A male subject, aged 63 to 67 · a dermatoscopic image of a skin lesion:
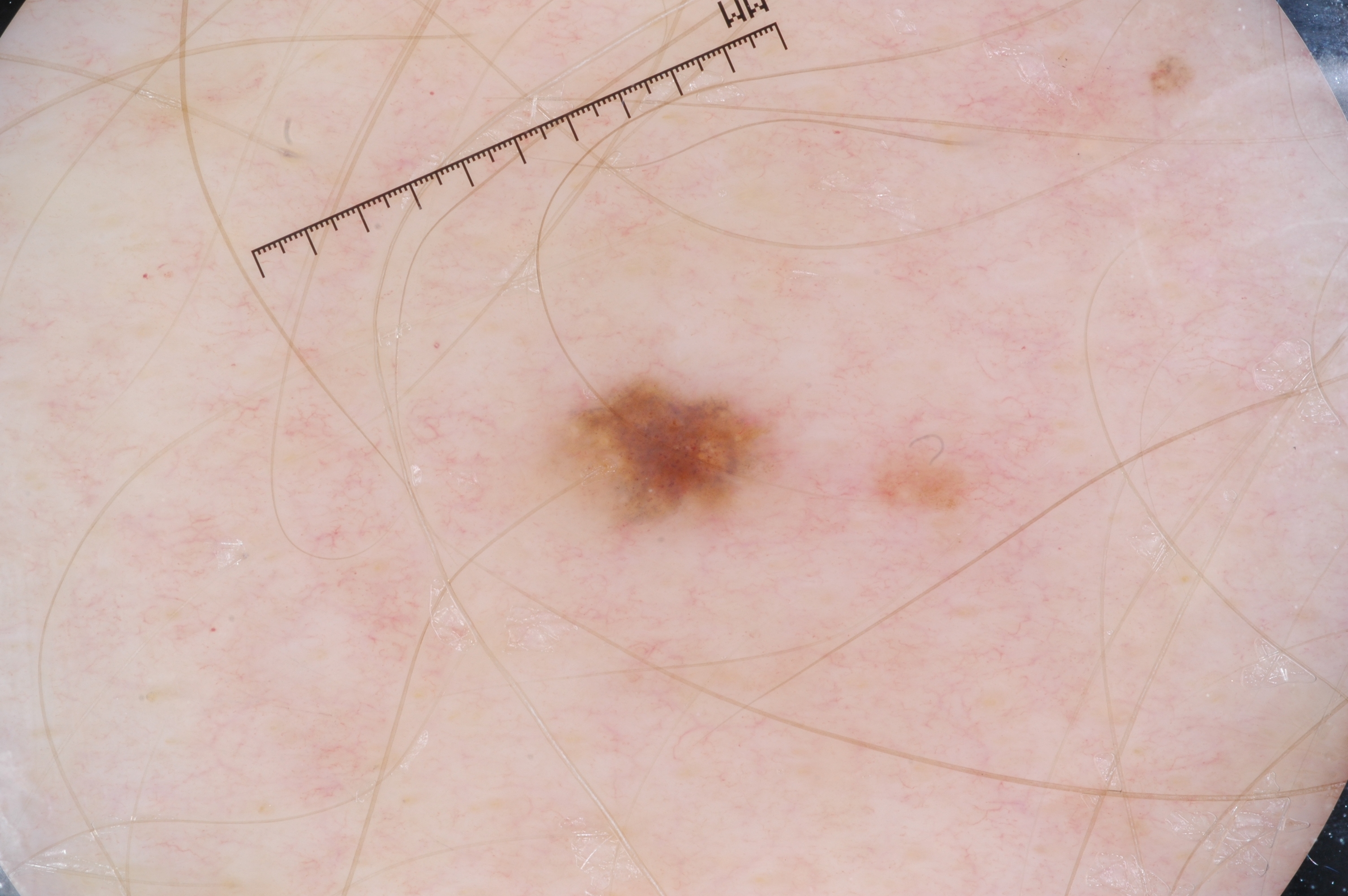Q: What is the lesion's bounding box?
A: <box>548, 371, 779, 532</box>
Q: How large is the lesion within the image?
A: small
Q: What does dermoscopy show?
A: milia-like cysts; absent: streaks, pigment network, and negative network
Q: What is this lesion?
A: a melanocytic nevus, a benign lesion